The affected area is the palm · close-up view.
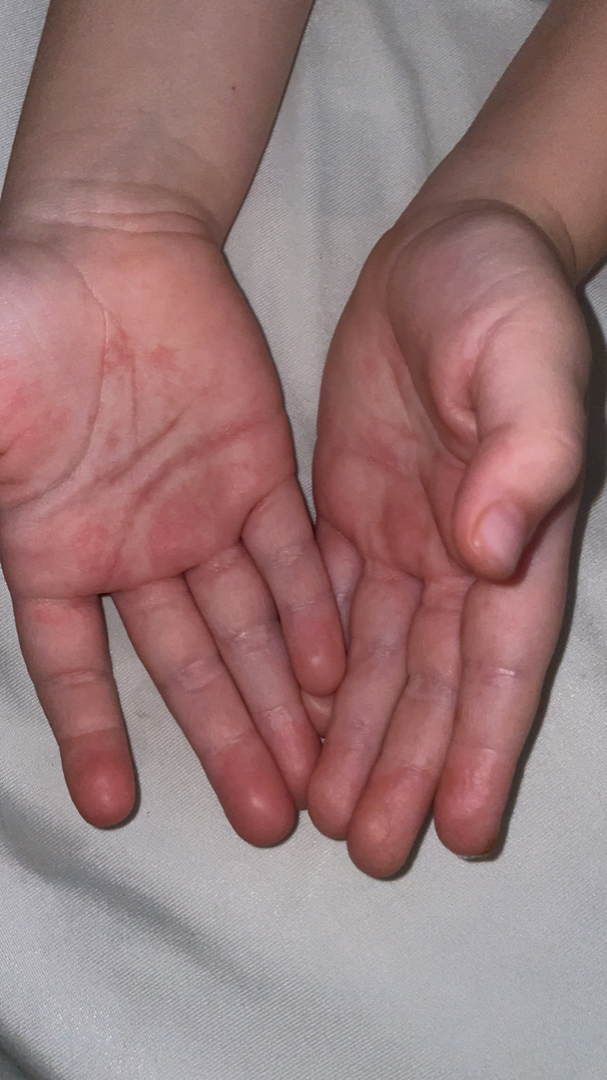The lesion is described as flat. The lesion is associated with itching. Present for one to four weeks. On dermatologist assessment of the image, Viral Exanthem (weight 0.41); Hand foot and mouth disease (weight 0.41); Eczema (weight 0.18).